Dermoscopy of a skin lesion: 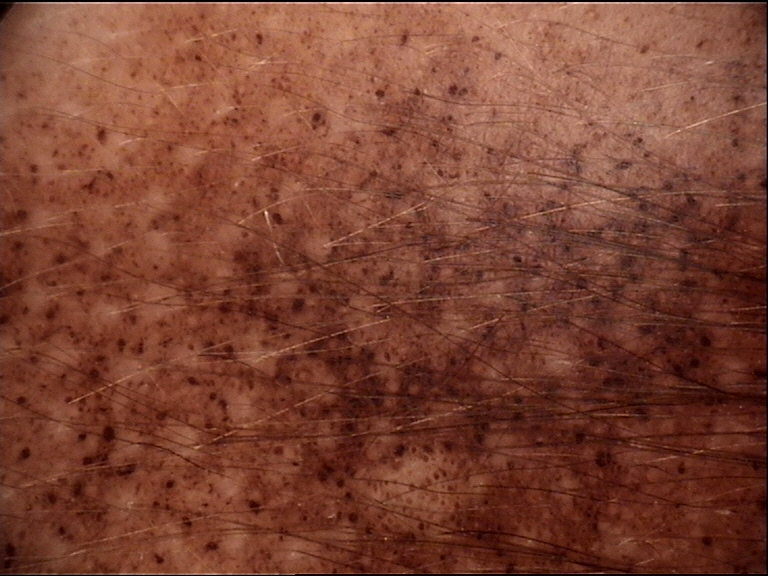Classified as a banal lesion — a congenital compound nevus.